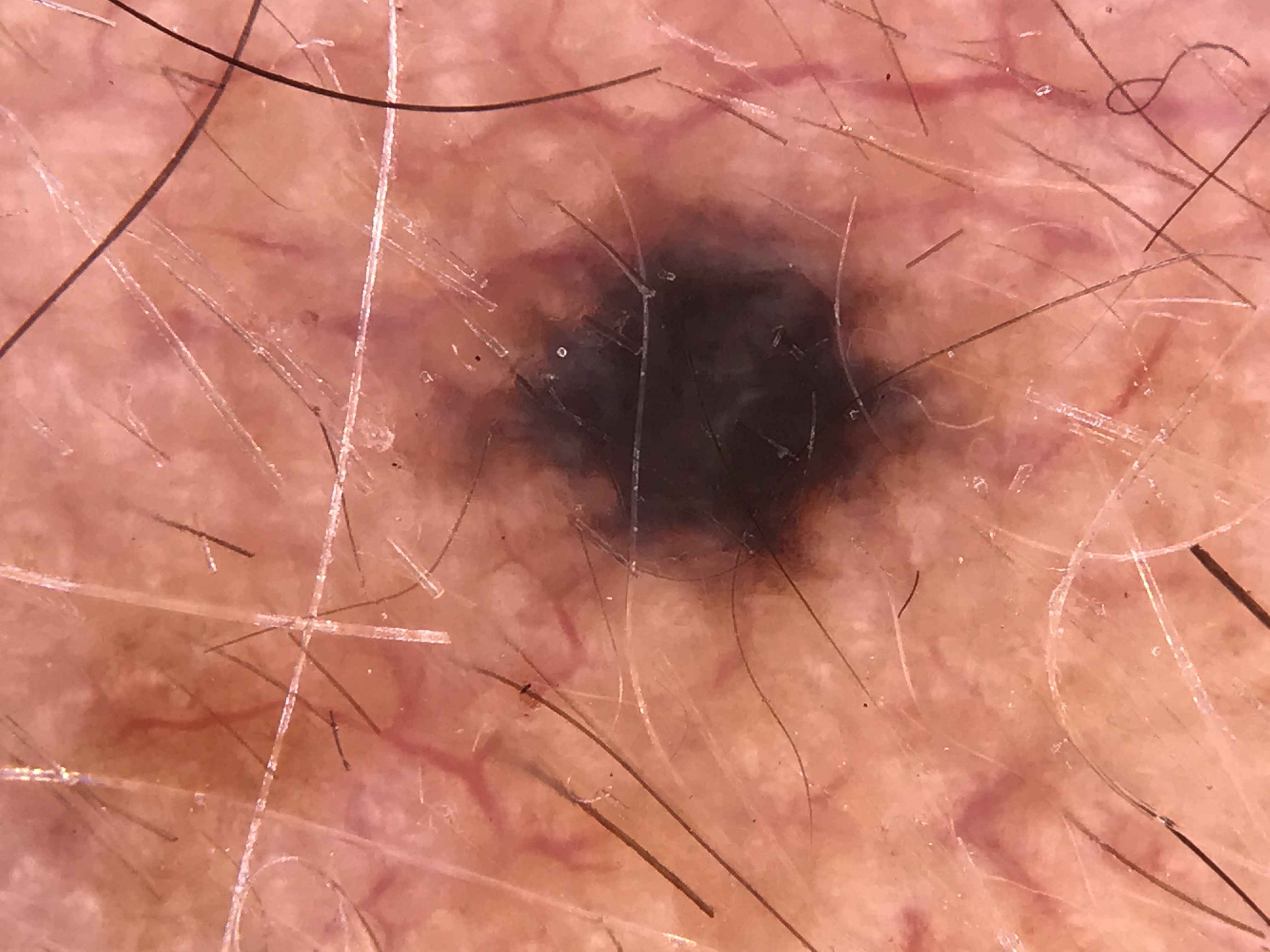{"diagnosis": {"name": "blue nevus", "code": "bdb", "malignancy": "benign", "super_class": "melanocytic", "confirmation": "expert consensus"}}